A clinical photo of a skin lesion taken with a smartphone. A subject in their early 40s:
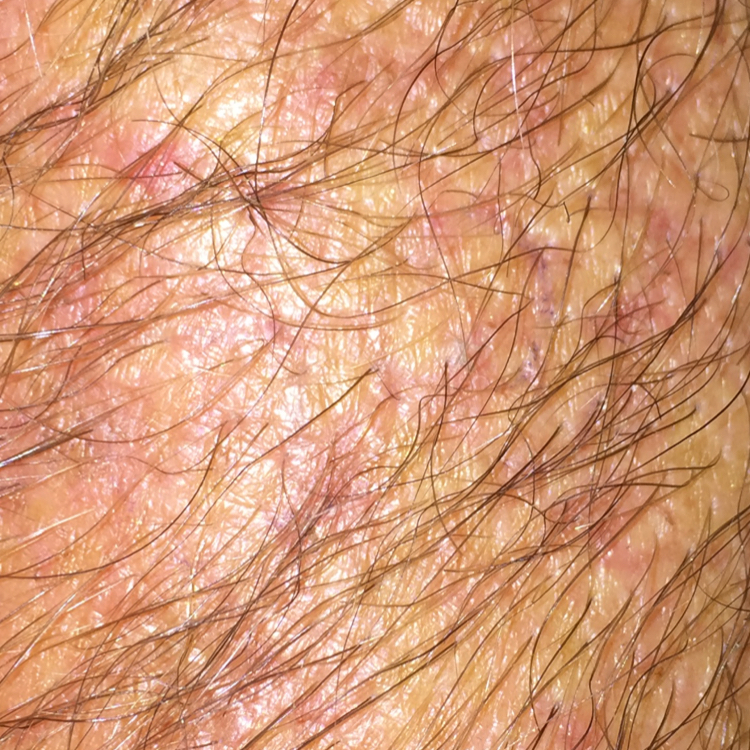| feature | finding |
|---|---|
| body site | an arm |
| symptoms | bleeding, itching / no elevation, no change in appearance |
| diagnosis | actinic keratosis (clinical consensus) |